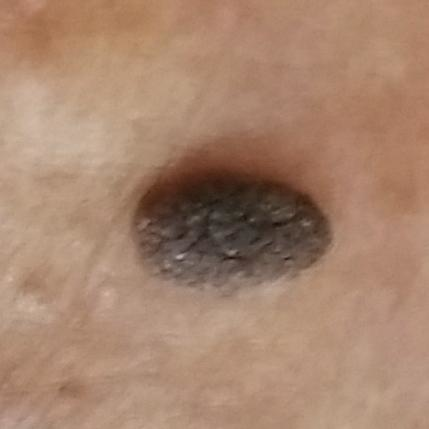  image: smartphone clinical photo
  symptoms:
    present:
      - growth
      - elevation
  diagnosis:
    name: seborrheic keratosis
    code: SEK
    malignancy: benign
    confirmation: clinical consensus